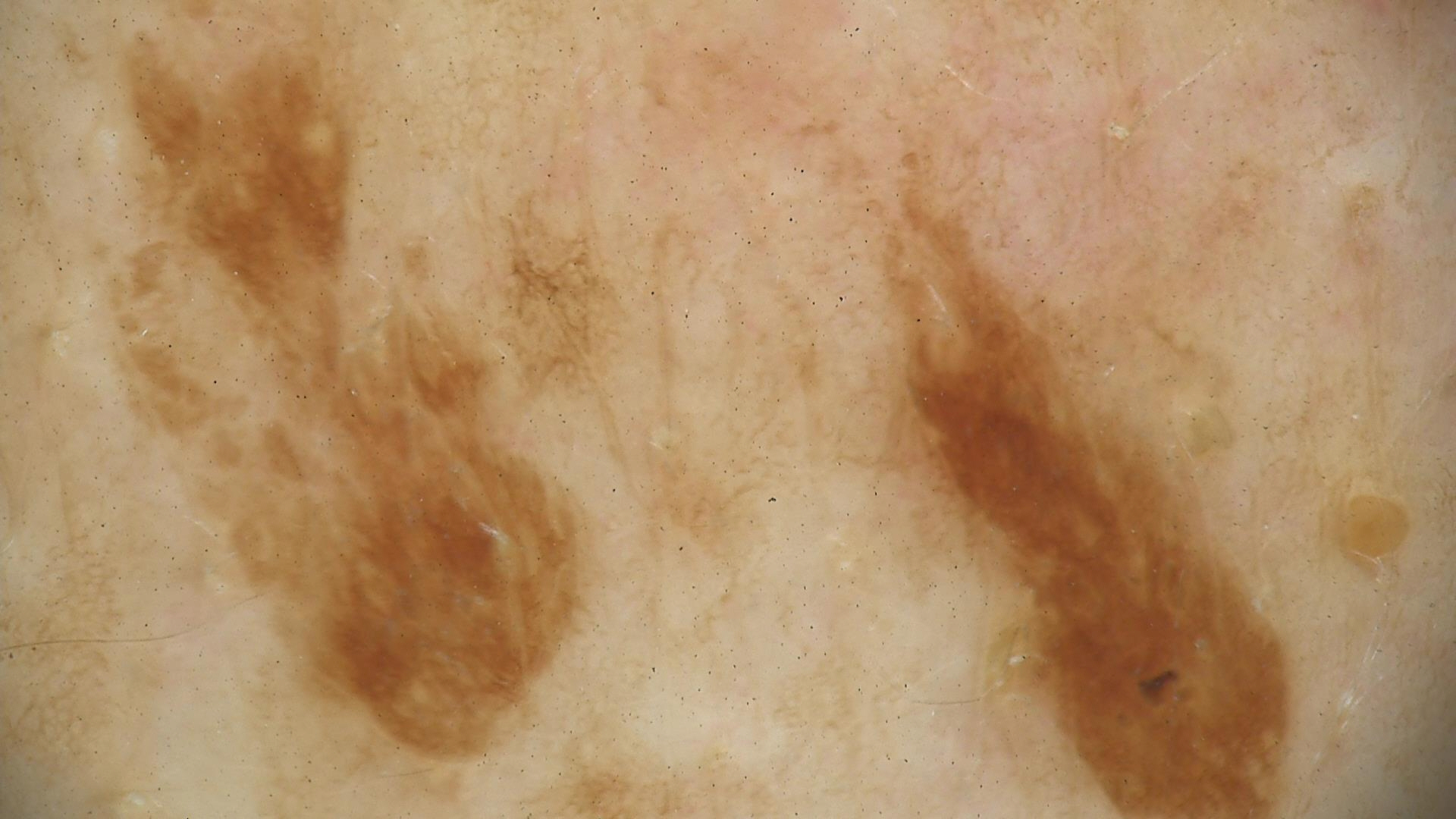The diagnostic label was a seborrheic keratosis.